The condition has been present for less than one week · symptoms reported: itching · the patient described the issue as a rash · skin tone: Fitzpatrick skin type I · the affected area is the leg · a close-up photograph:
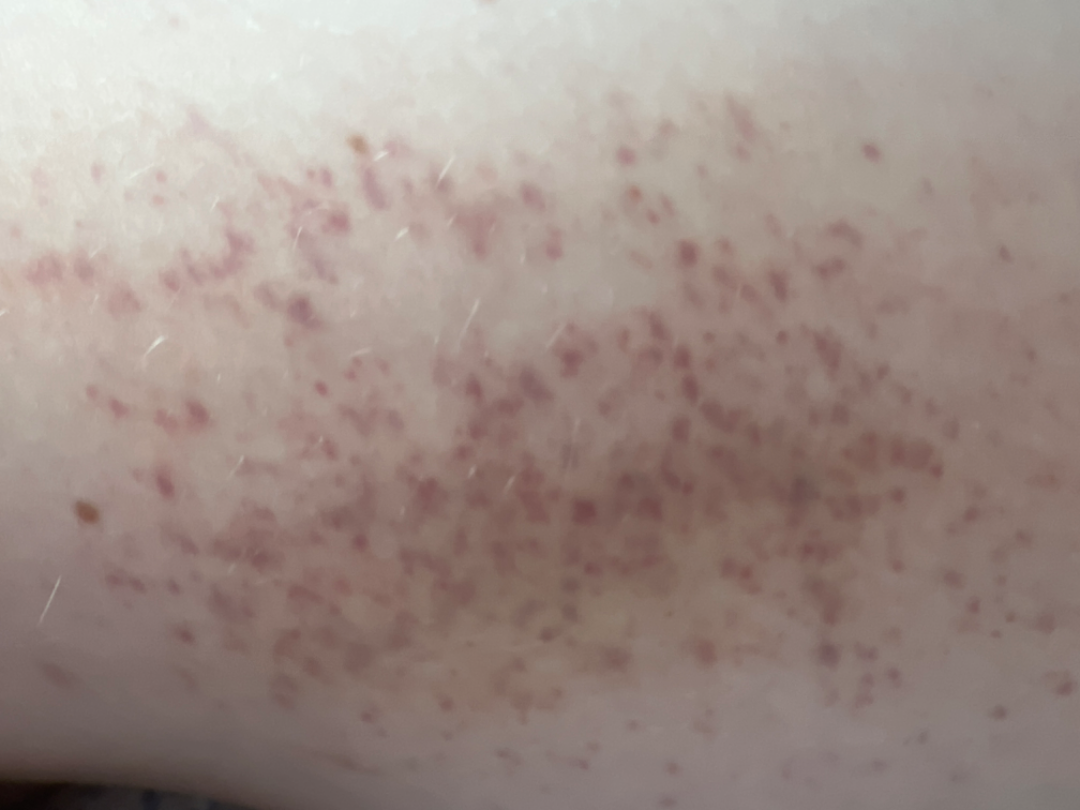Review: On dermatologist assessment of the image: the differential is split between Pigmented purpuric eruption, Eczema and Allergic Contact Dermatitis.